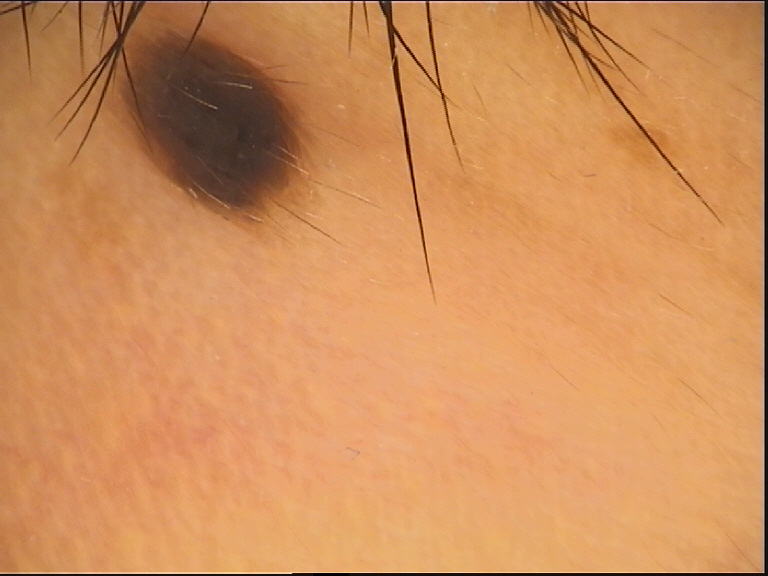A dermoscopy image of a single skin lesion. The diagnostic label was a banal lesion — a compound nevus.